A dermoscopic image of a skin lesion: 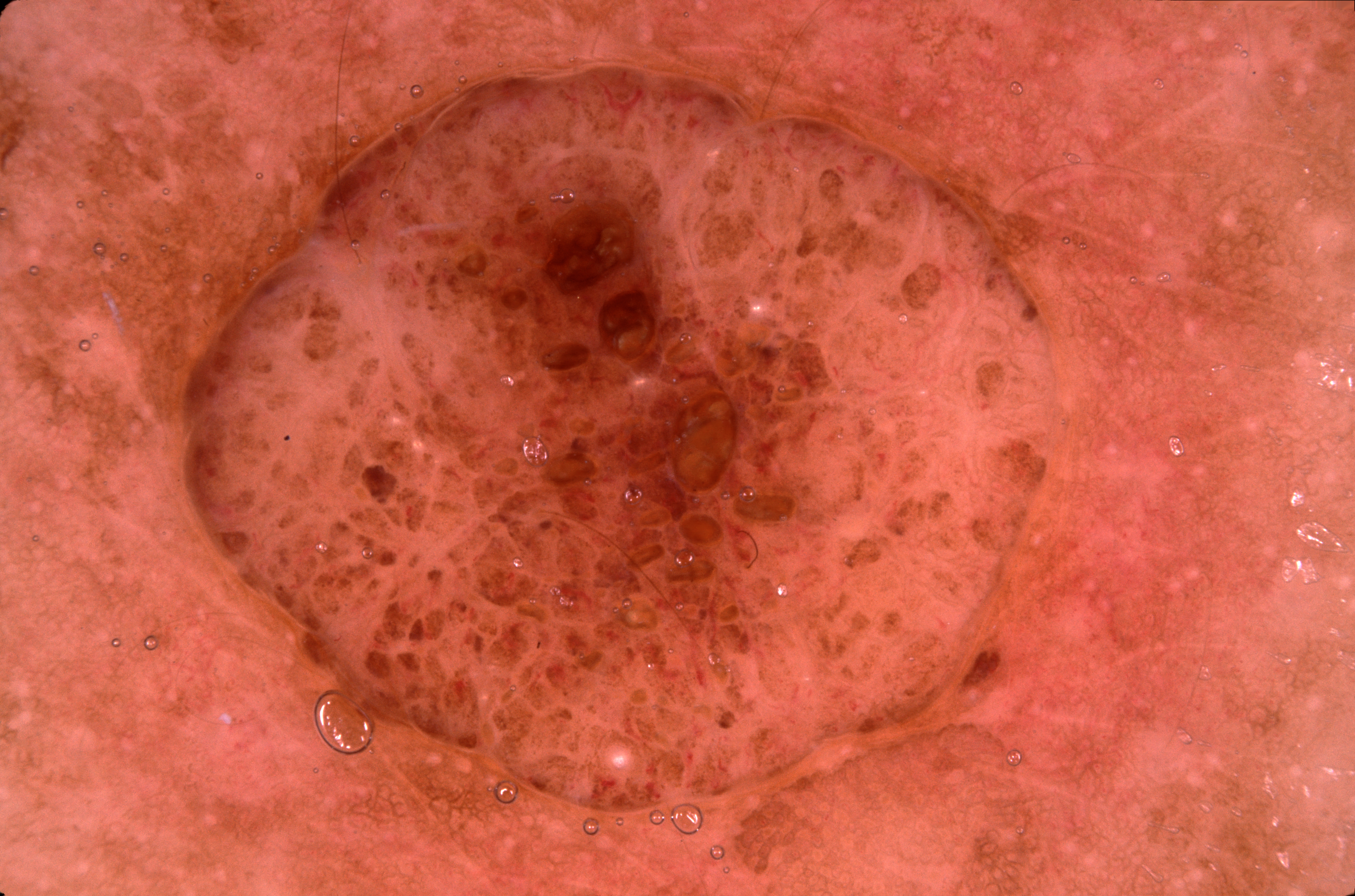A prominent lesion filling much of the field.
On dermoscopy, the lesion shows milia-like cysts, with no pigment network, streaks, or negative network.
As (left, top, right, bottom), lesion location: [164,42,1107,825].
The lesion was assessed as a melanocytic nevus.